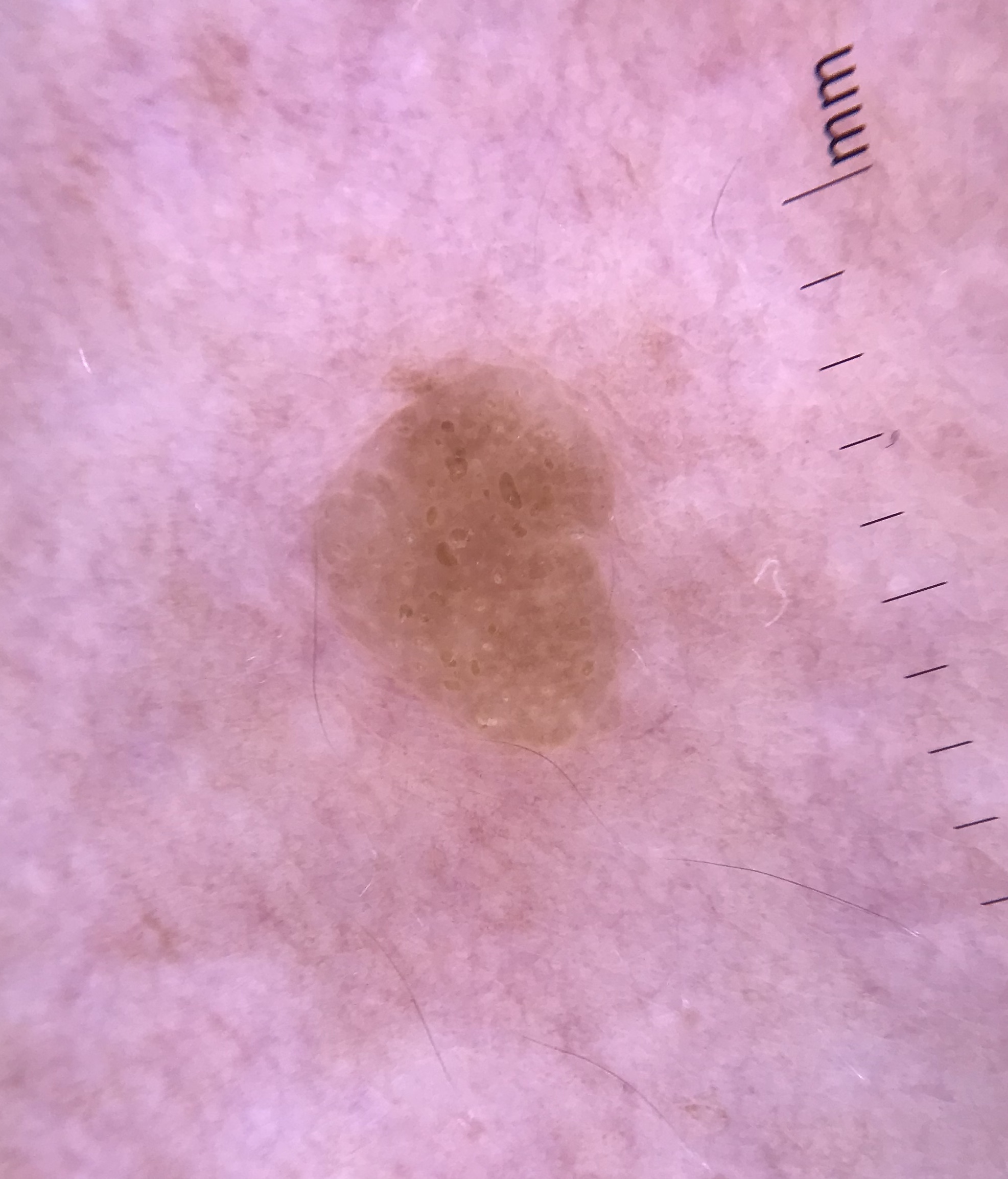label=seborrheic keratosis (expert consensus).